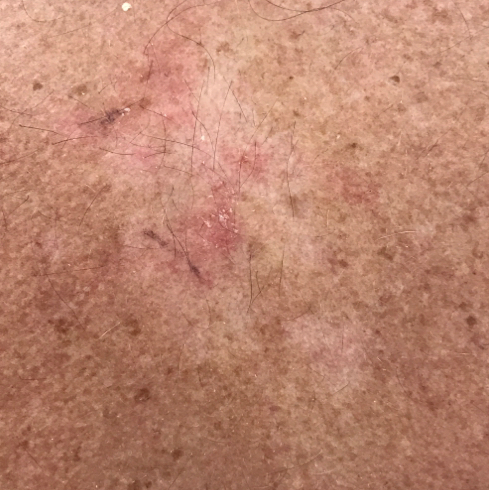patient = 63 years of age
image type = smartphone clinical photo
region = the back
reported symptoms = itching, growth
diagnosis = actinic keratosis (clinical consensus)